The patient reports the condition has been present for less than one week · the lesion is described as fluid-filled · the patient reports bothersome appearance, burning, pain and itching · male contributor, age 30–39 · skin tone: FST II; lay reviewers estimated 2 on the Monk Skin Tone · the patient described the issue as a rash · the lesion involves the arm · the photograph is a close-up of the affected area · the patient reported no systemic symptoms:
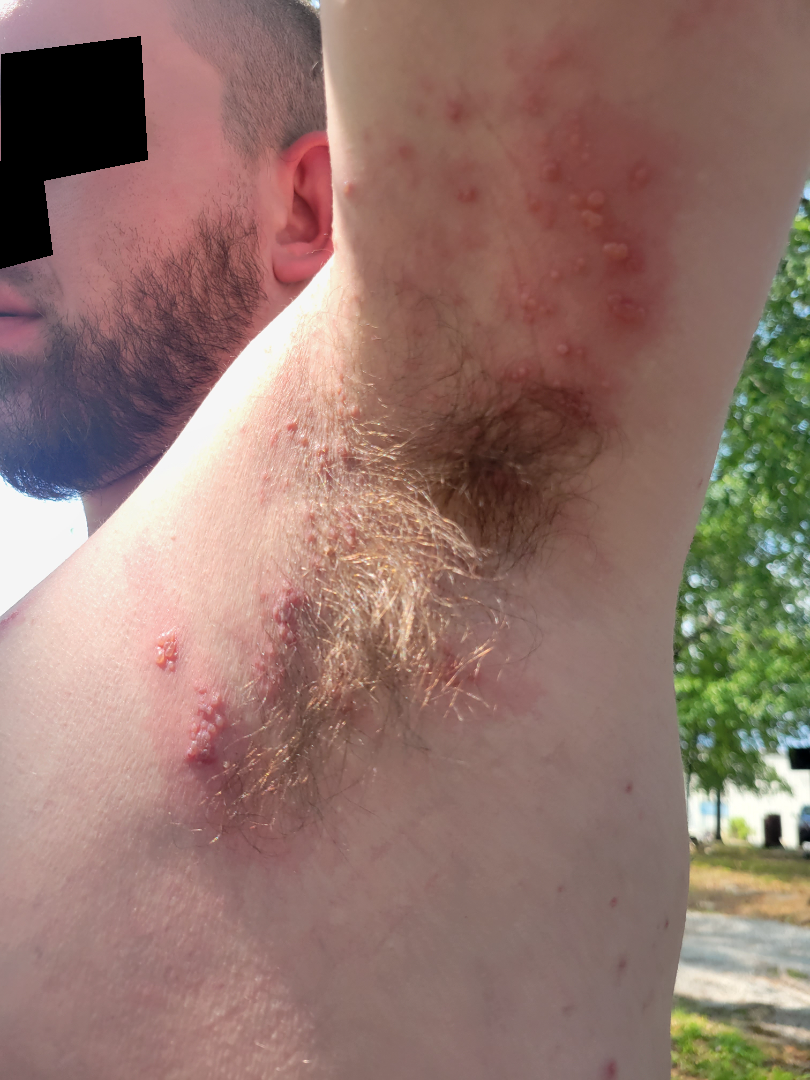Single-reviewer assessment: most likely Herpes Zoster; also on the differential is Hidradenitis; also consider Allergic Contact Dermatitis.